An image taken at a distance. The affected area is the front of the torso, back of the torso, leg and arm:
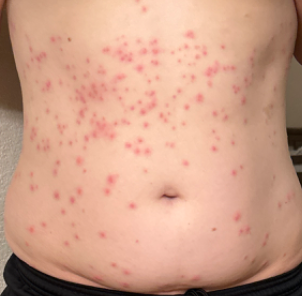Impression:
Most consistent with Insect Bite.